Located on the head or neck · a close-up photograph · the patient is male: 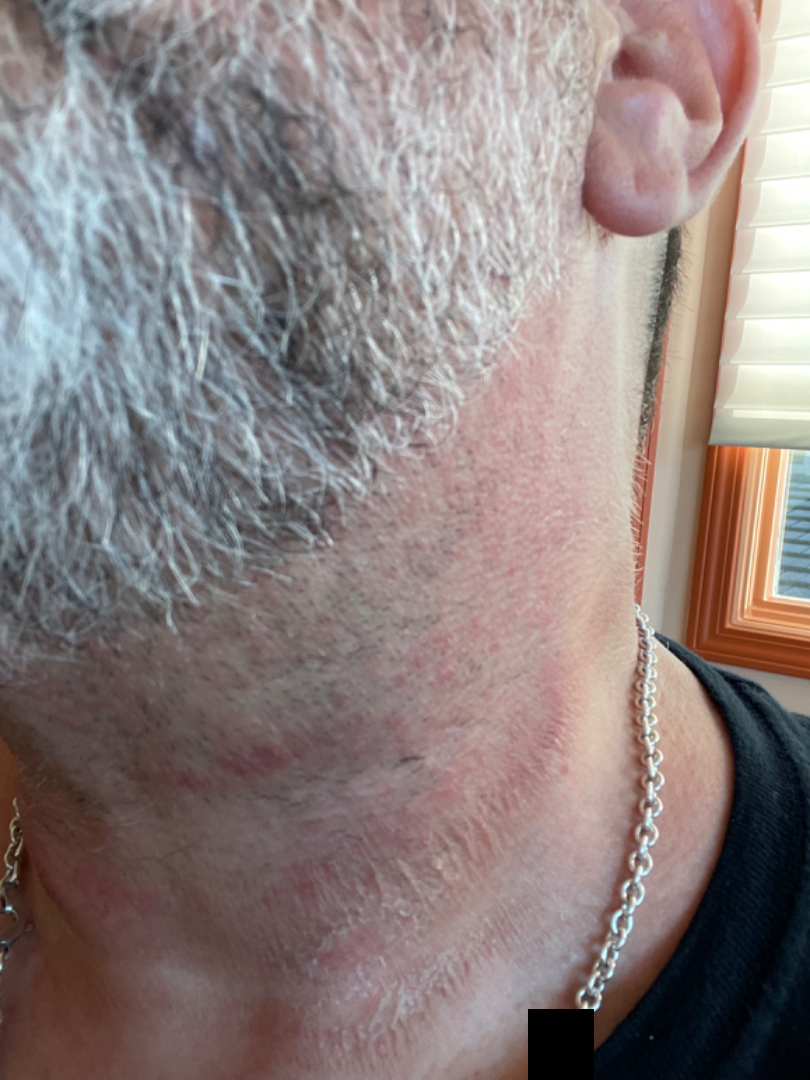{"texture": "rough or flaky", "patient_category": "a rash", "skin_tone": {"fitzpatrick": "II", "monk_skin_tone": 2}, "differential": {"leading": ["Allergic Contact Dermatitis"], "unlikely": ["Contact dermatitis, NOS", "Eczema", "Tinea", "Irritant Contact Dermatitis", "Photodermatitis"]}}